A female subject 35 years old; the patient describes having a moderate number of moles; a skin lesion imaged with a dermatoscope; on a questionnaire the patient reported no personal history of cancer; the patient says their skin reddens painfully with sun exposure; imaged for a research study, with no referral diagnosis recorded.
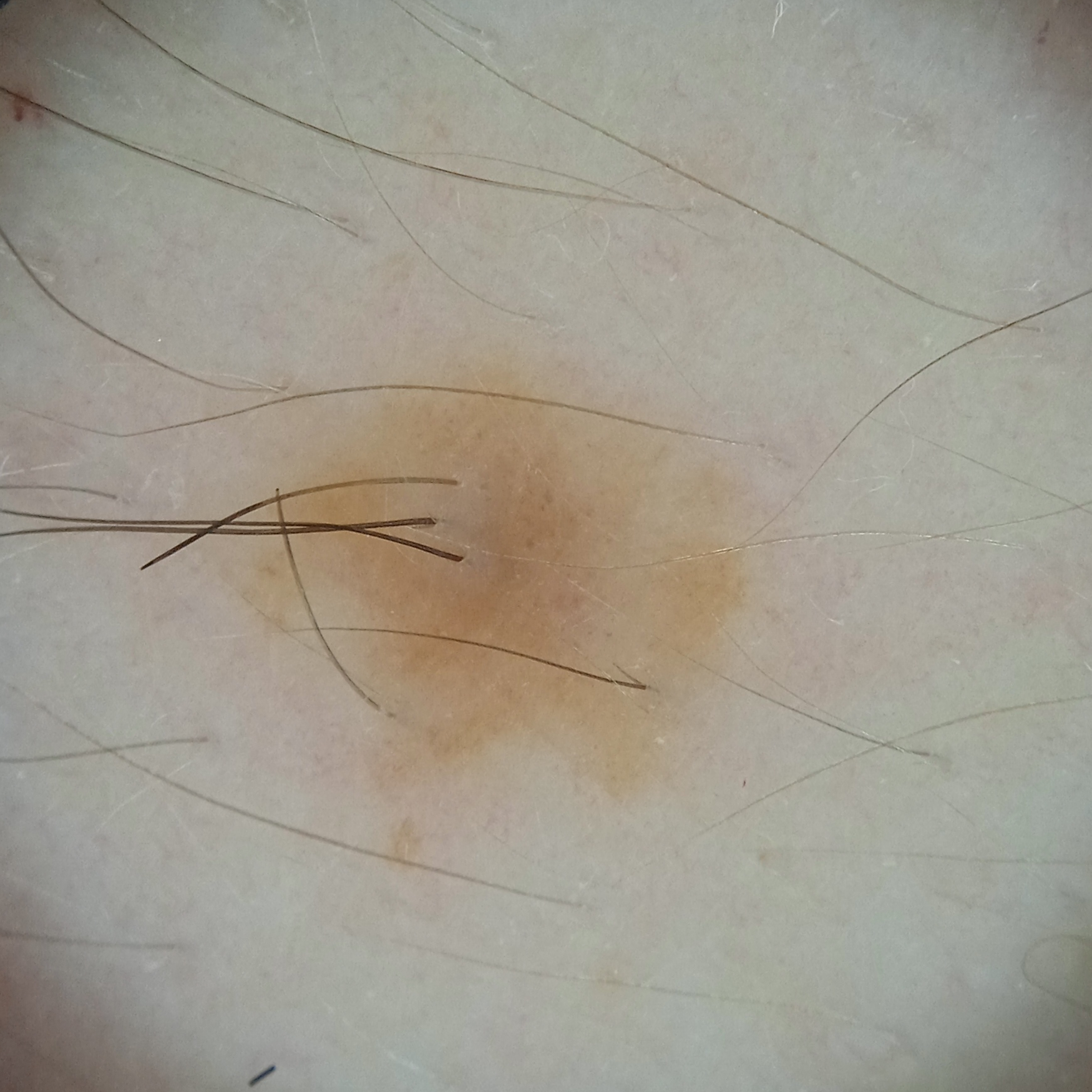Q: What is the anatomic site?
A: an arm
Q: How large is the lesion?
A: 5.8 mm
Q: What was the diagnosis?
A: melanocytic nevus (dermatologist consensus)